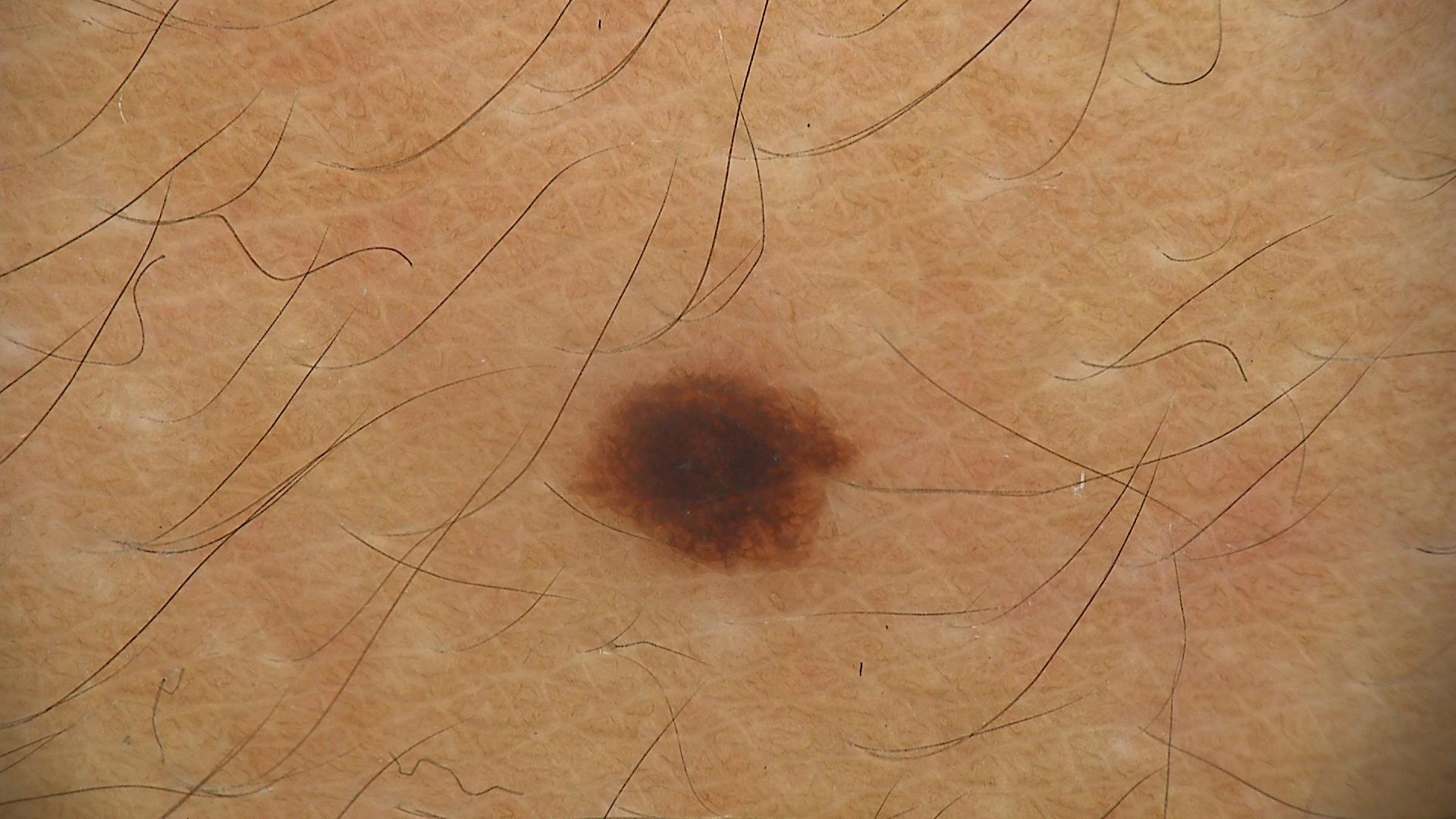Classified as a dysplastic junctional nevus.